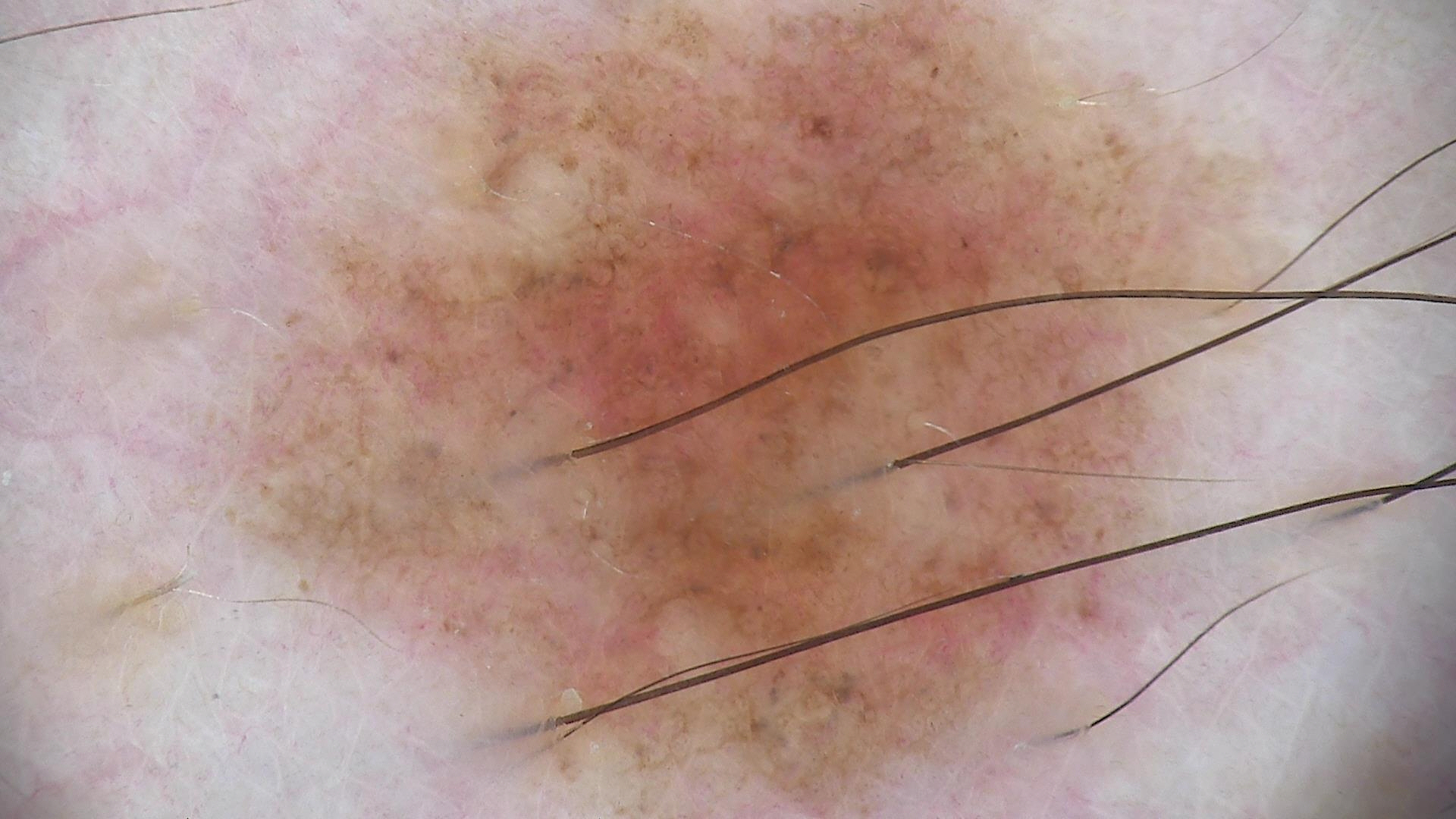  diagnosis:
    name: dysplastic compound nevus
    code: cd
    malignancy: benign
    super_class: melanocytic
    confirmation: expert consensus